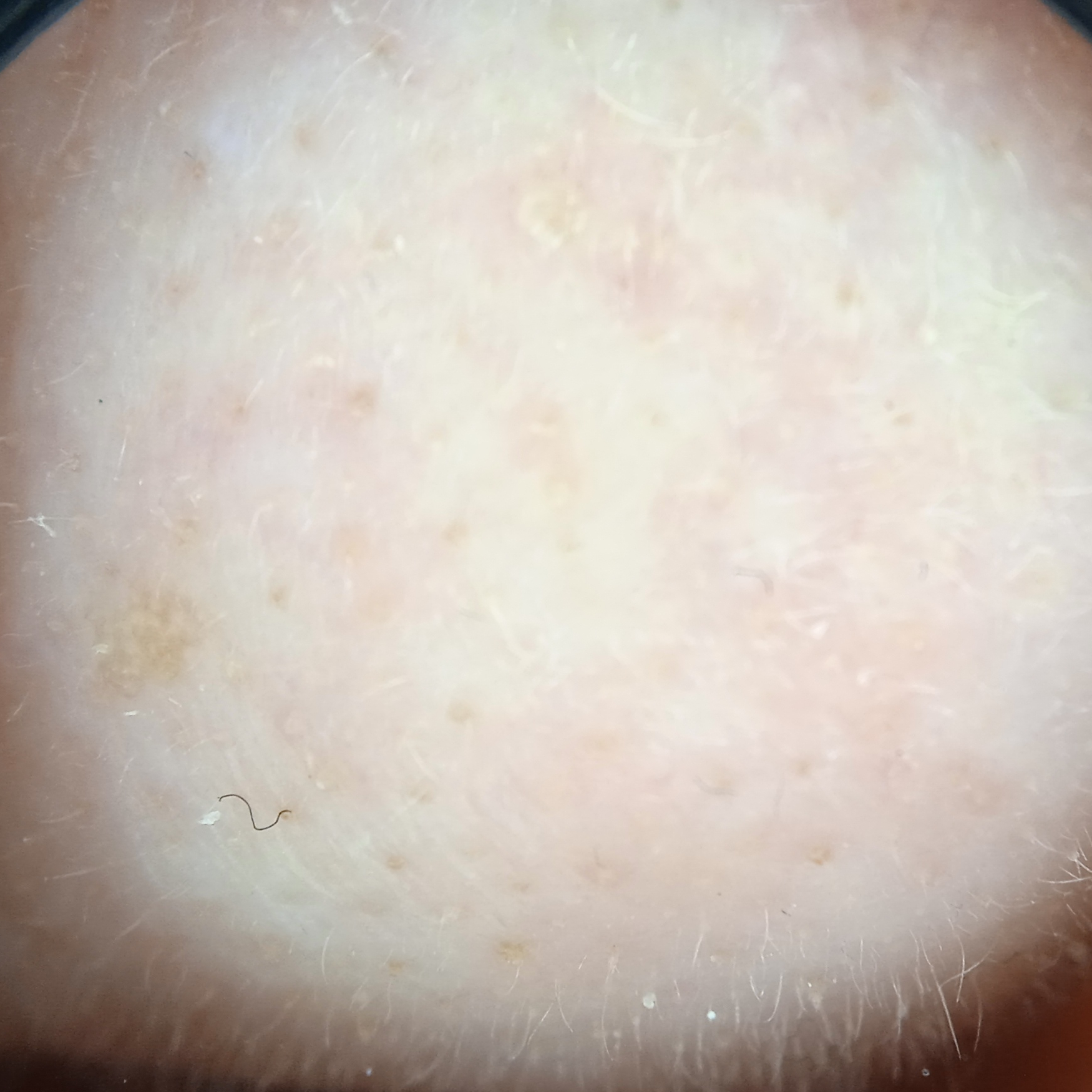A female patient 71 years of age. The referring clinician suspected basal cell carcinoma. A skin lesion imaged with a dermatoscope. The lesion measures approximately 7.3 mm. Dermatologist review favored an actinic keratosis.